Skin tone: human graders estimated MST 2–3 · the lesion involves the arm · reported lesion symptoms include itching · the lesion is described as rough or flaky and raised or bumpy · female subject, age 50–59 · the photograph is a close-up of the affected area · the patient described the issue as a rash · the condition has been present for one to four weeks — 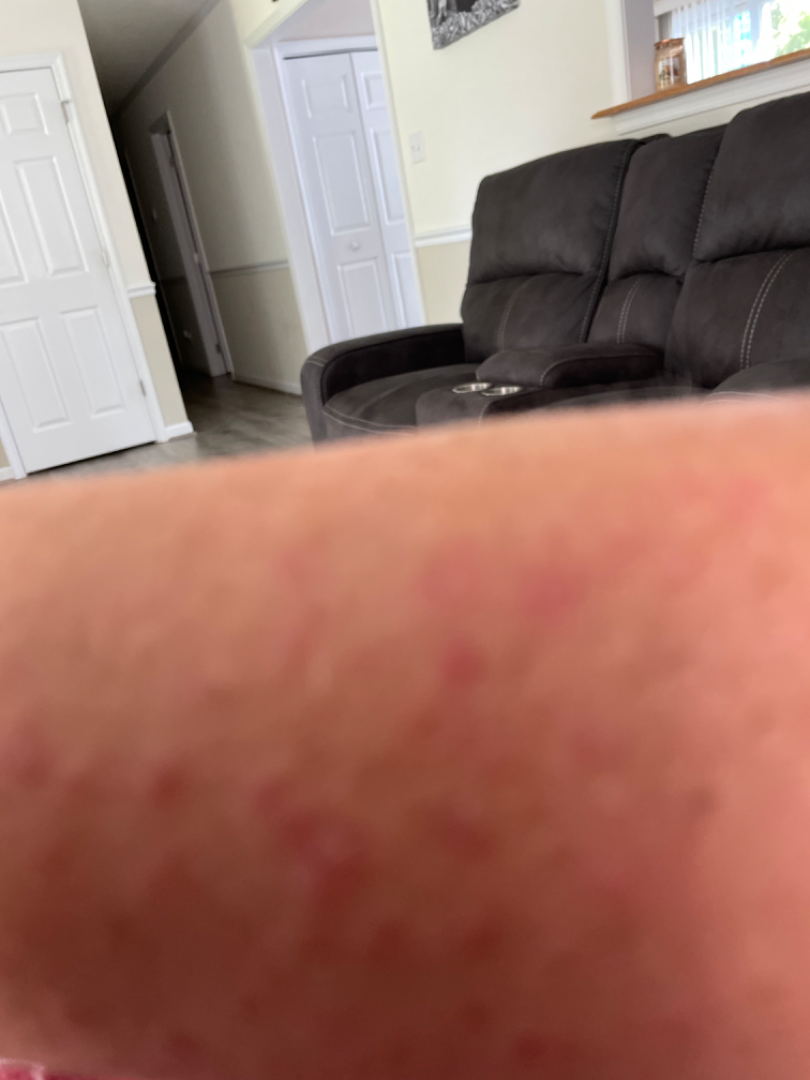  assessment: indeterminate from the photograph